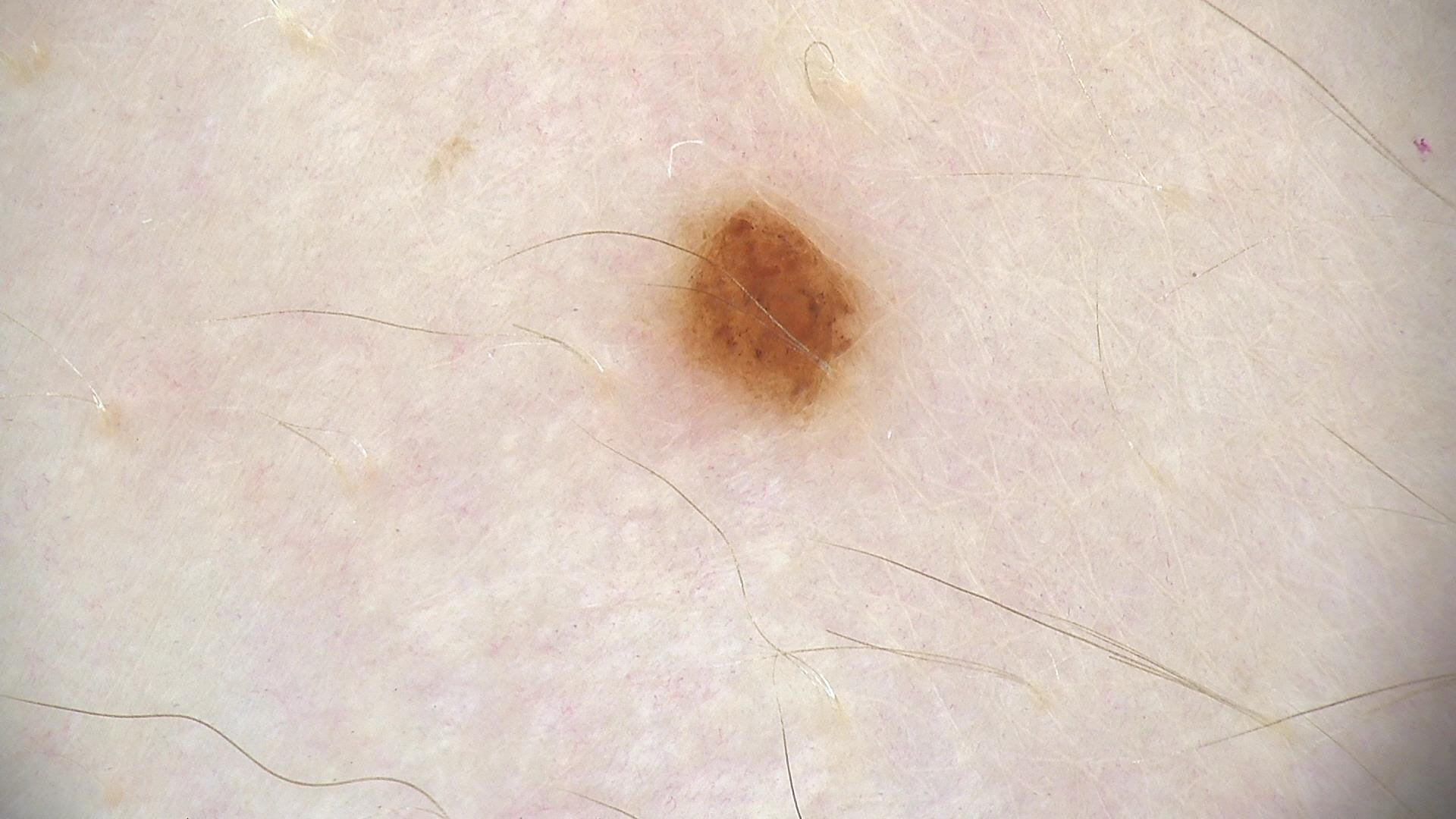Q: What is this lesion?
A: dysplastic junctional nevus (expert consensus)